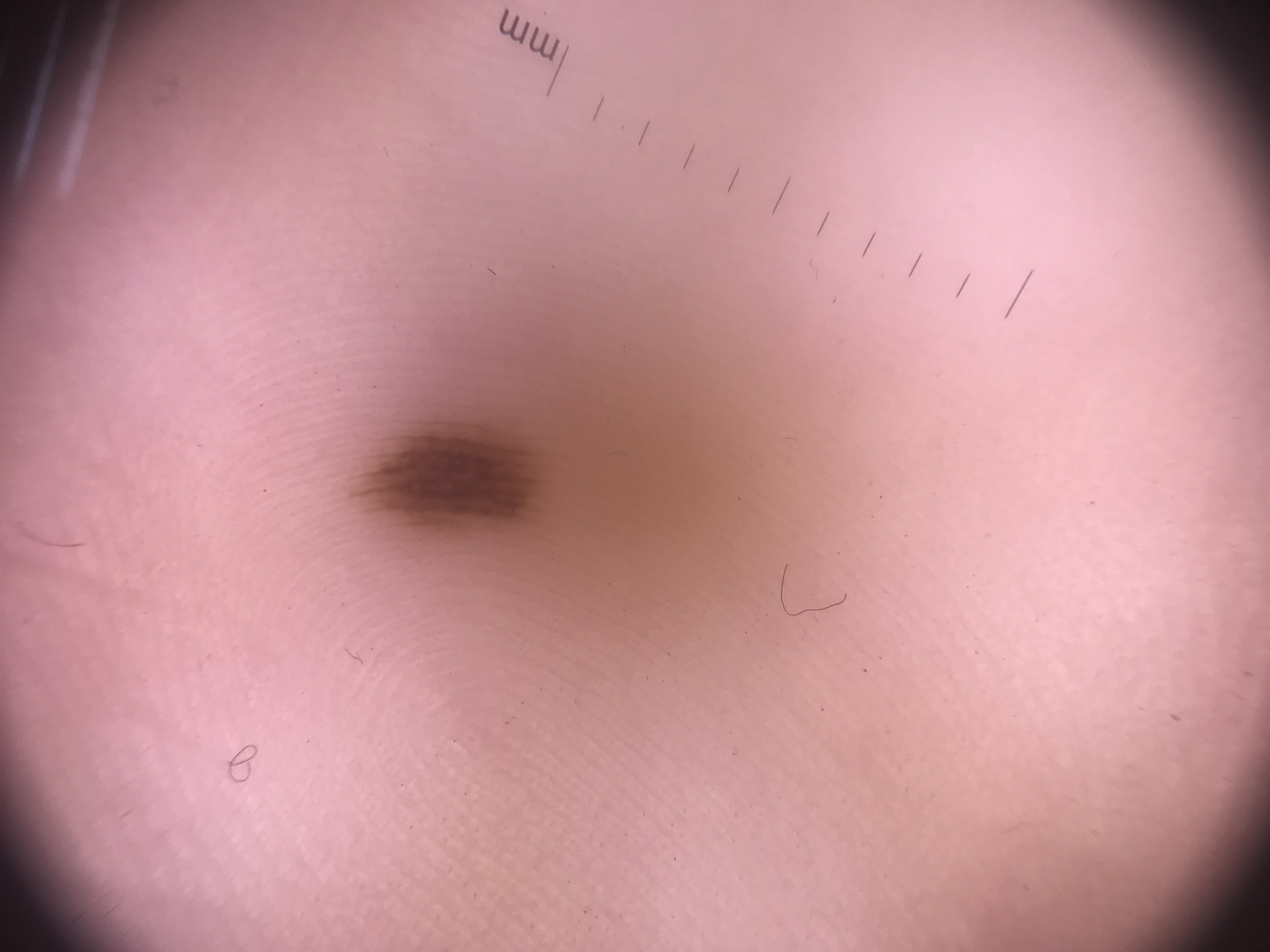Summary:
A skin lesion imaged with a dermatoscope. The architecture is that of a banal lesion.
Impression:
The diagnosis was an acral junctional nevus.